An image taken at an angle; the contributor reports the condition has been present for one to four weeks; located on the front of the torso, head or neck, leg and arm; the subject is 60–69, female; the patient considered this a rash: 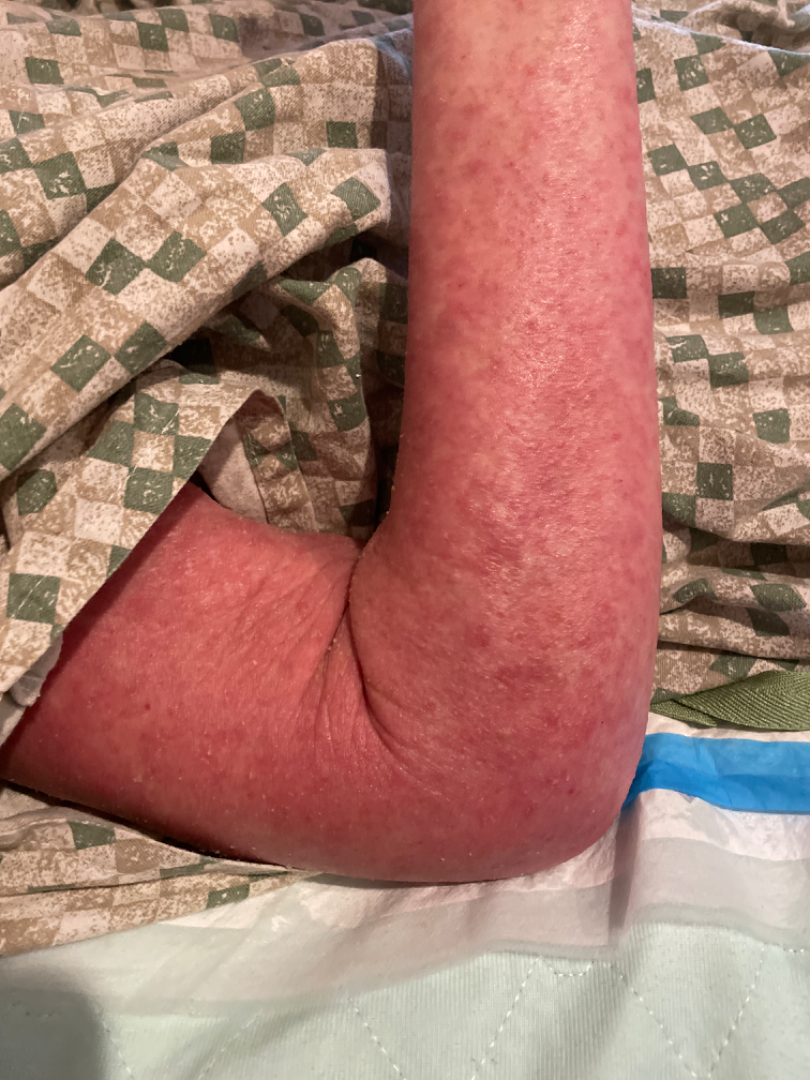  assessment: could not be assessed